Reported lesion symptoms include itching · the patient considered this a rash · the lesion involves the front of the torso, arm, back of the hand and leg · the photograph is a close-up of the affected area · texture is reported as flat · present for one to four weeks:
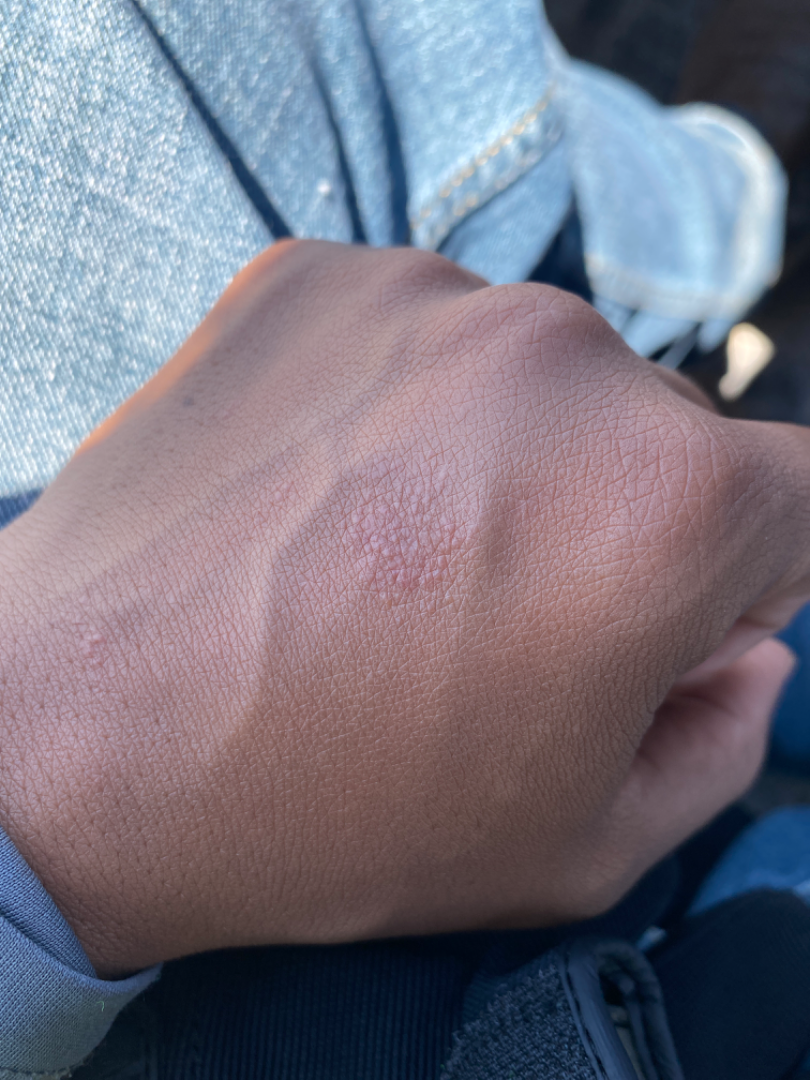The reviewer was unable to grade this case for skin condition.